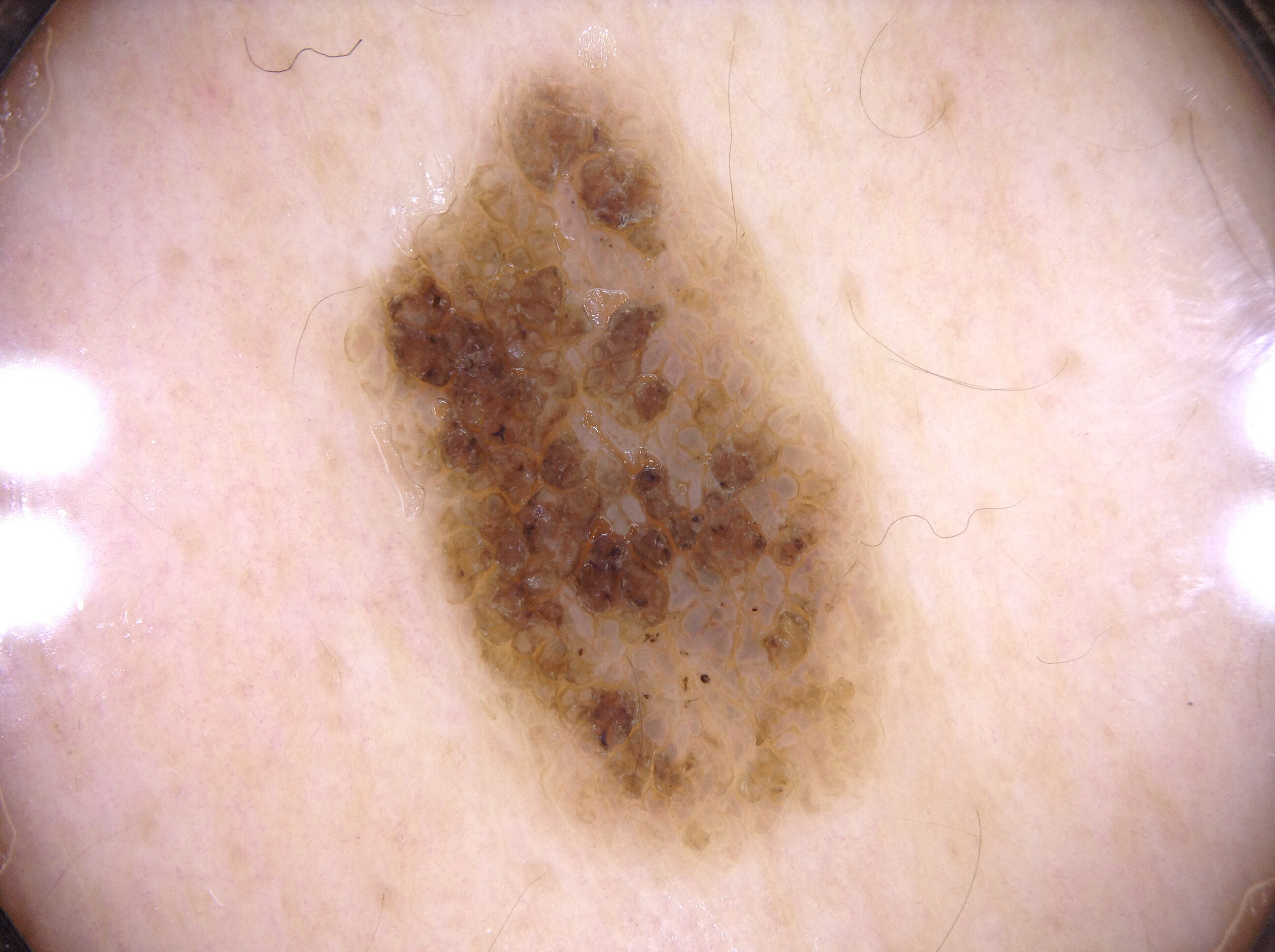A dermoscopic close-up of a skin lesion.
The lesion's extent is [359, 75, 887, 855].
On dermoscopy, the lesion shows no streaks, milia-like cysts, negative network, or pigment network.
The lesion occupies roughly 22% of the field.
Clinically diagnosed as a seborrheic keratosis, a benign skin lesion.